The photo was captured at an angle: 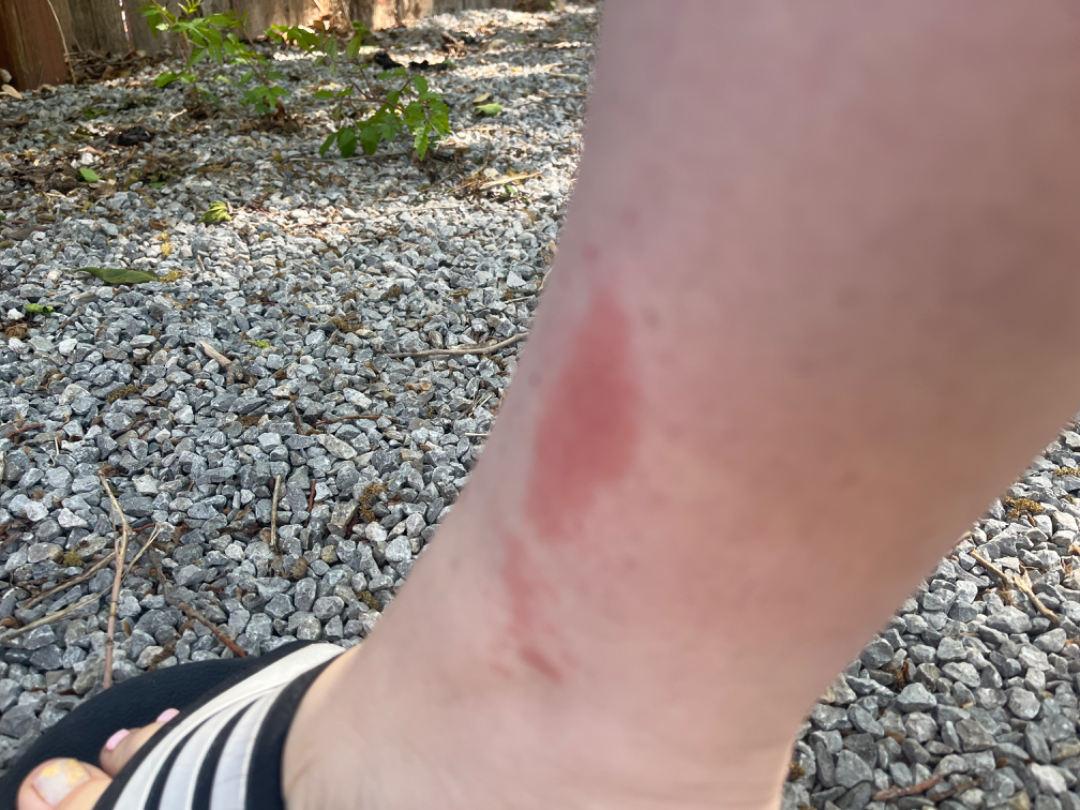Background: Fitzpatrick II. Findings: On dermatologist assessment of the image: Allergic Contact Dermatitis (considered); Irritant Contact Dermatitis (considered).